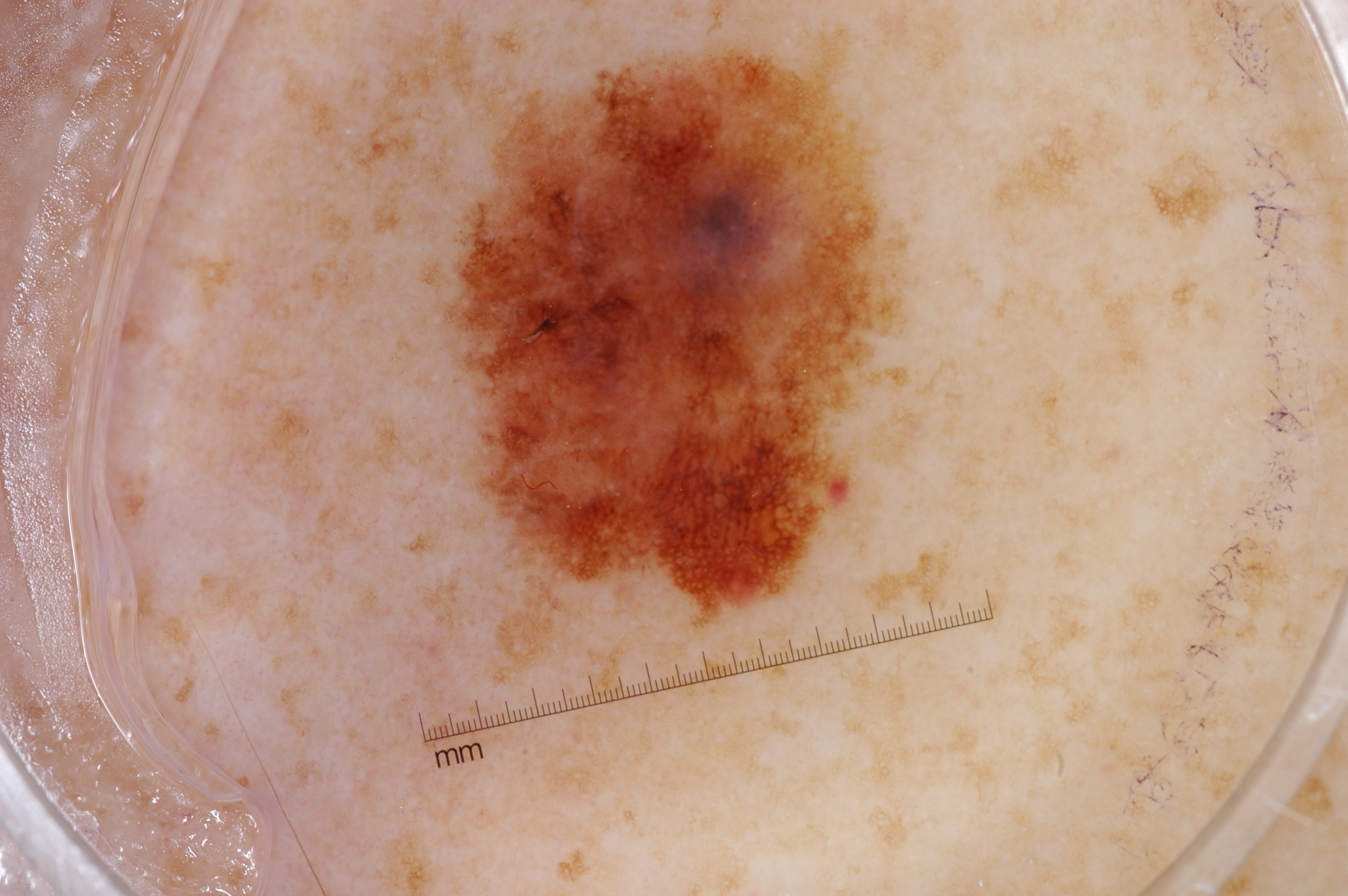Q: What is the imaging modality?
A: dermatoscopic image of a skin lesion
Q: Who is the patient?
A: male, aged around 60
Q: How much of the field does the lesion occupy?
A: ~15% of the field
Q: Which dermoscopic features were noted?
A: pigment network, milia-like cysts, and negative network
Q: Where is the lesion located?
A: bbox=[464, 56, 885, 602]
Q: What did the assessment conclude?
A: a melanoma